A dermoscopy image of a single skin lesion.
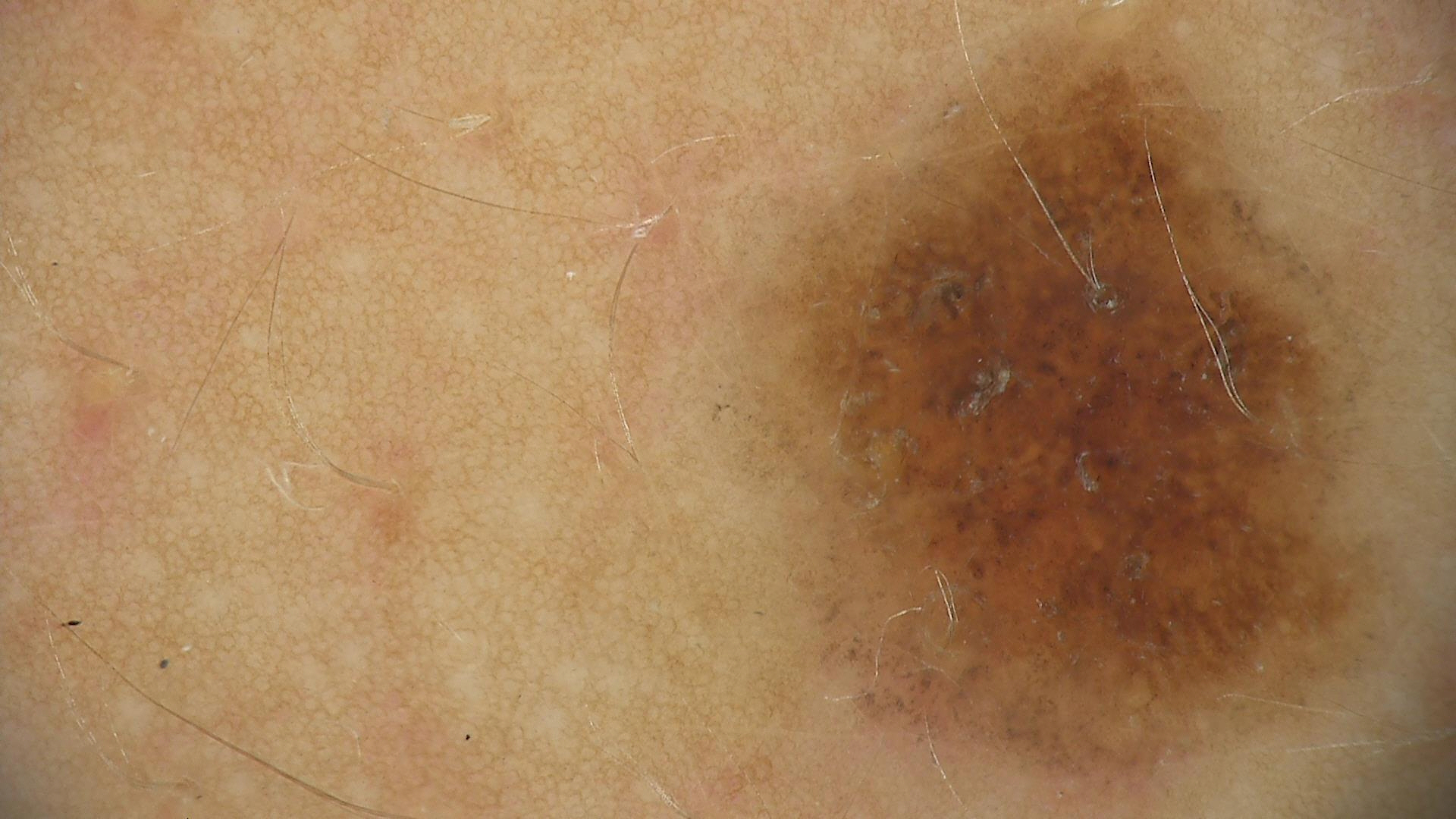The diagnostic label was a dysplastic junctional nevus.